Dermoscopy of a skin lesion.
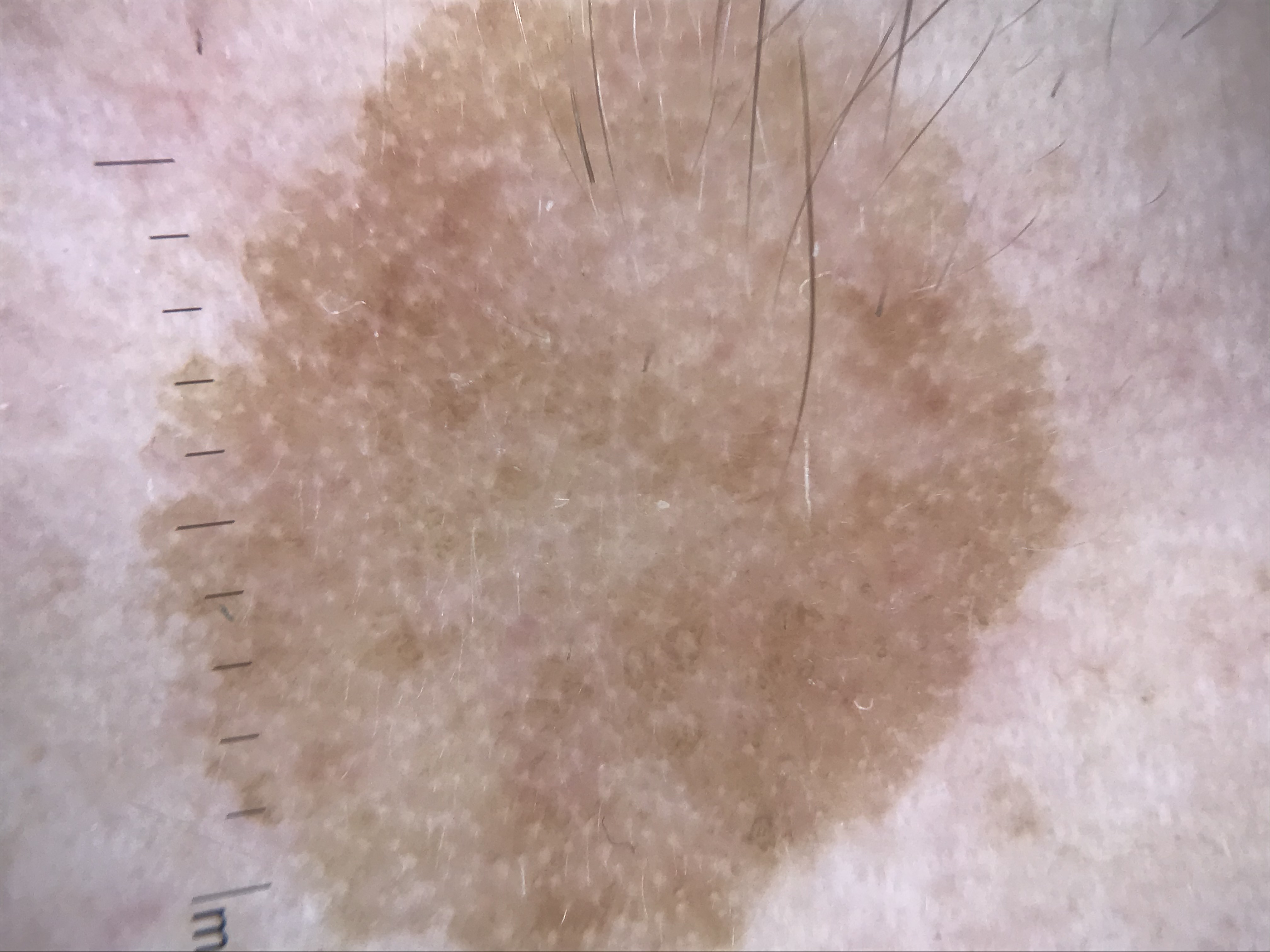lesion type — keratinocytic
label — seborrheic keratosis (expert consensus)